Located on the arm, back of the torso, head or neck and leg. An image taken at an angle — 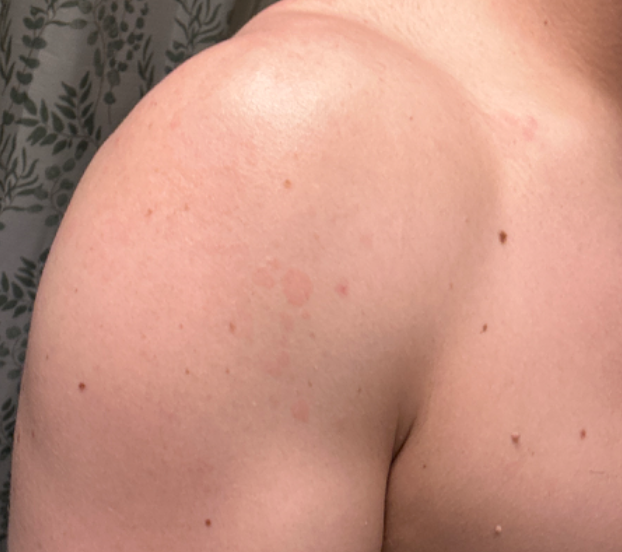Review:
Single-reviewer assessment: most consistent with Tinea Versicolor.